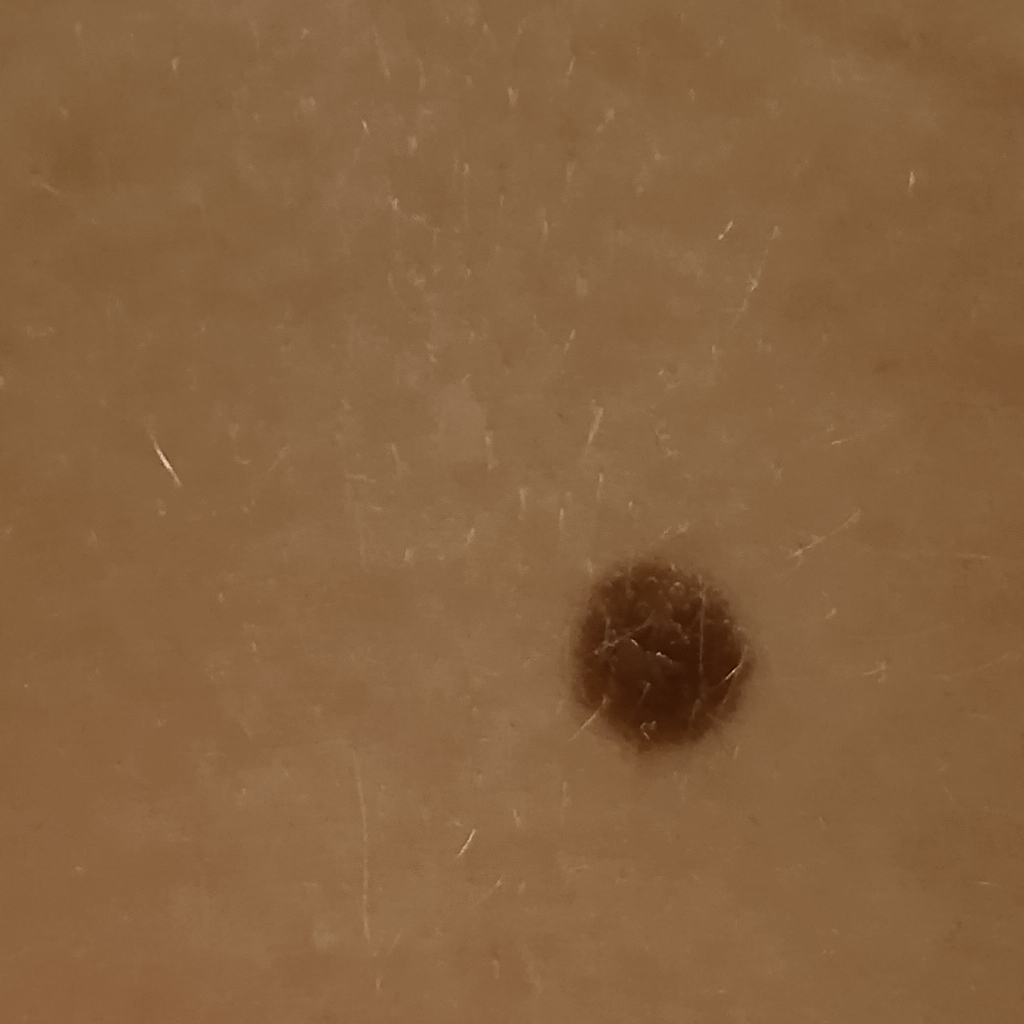Findings:
• referral · research study (no referral diagnosis)
• subject · female, age 26
• modality · clinical photo
• location · the back
• lesion size · 9.1 mm
• assessment · melanocytic nevus (dermatologist consensus)